A dermoscopic image of a skin lesion:
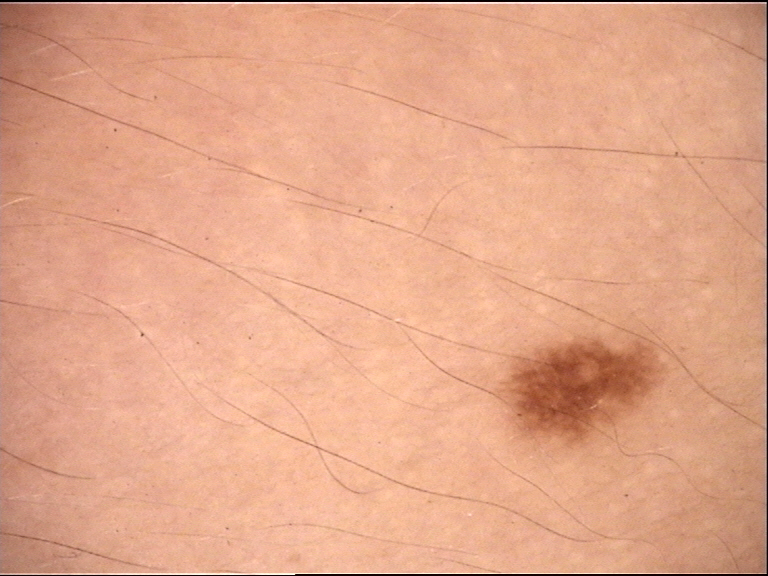This is a banal lesion. Diagnosed as a junctional nevus.